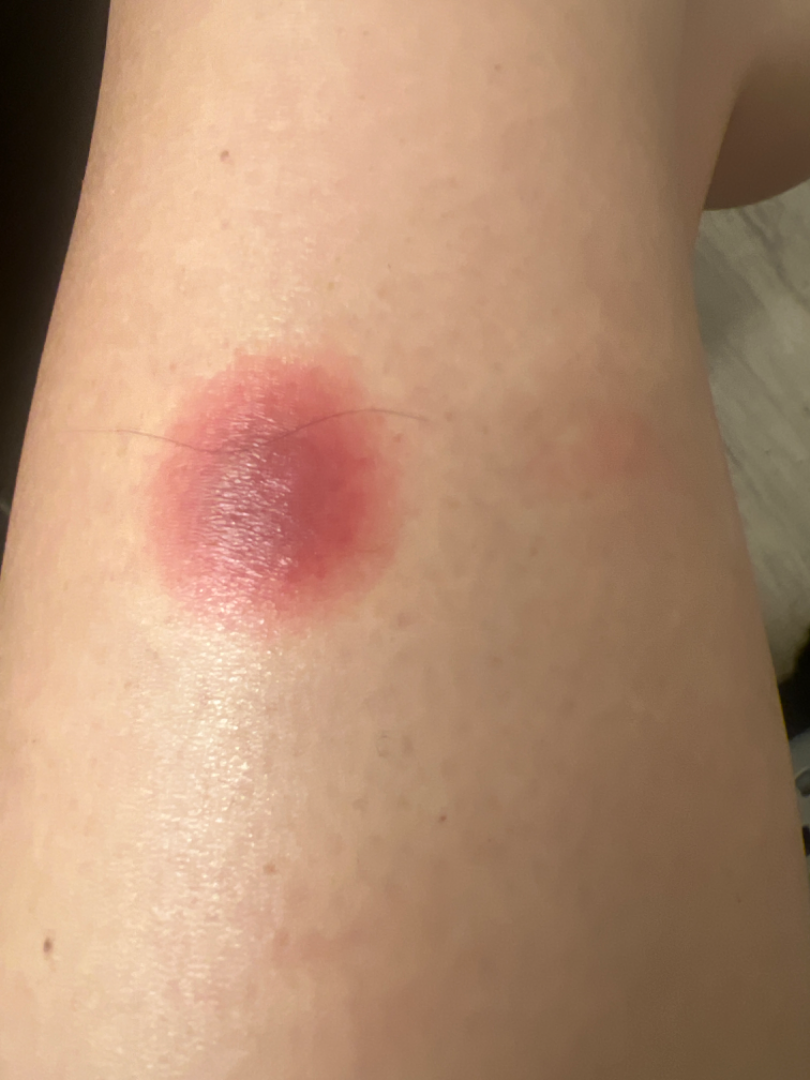| feature | finding |
|---|---|
| history | three to twelve months |
| lesion symptoms | bothersome appearance, darkening, itching and enlargement |
| subject | female |
| systemic symptoms | fatigue and chills |
| body site | leg and head or neck |
| skin tone | Fitzpatrick phototype III; lay graders estimated 3 on the Monk Skin Tone |
| photo taken | close-up |
| lesion texture | raised or bumpy and flat |
| patient's own categorization | a rash |
| differential diagnosis | the reviewer's impression was Drug Rash |